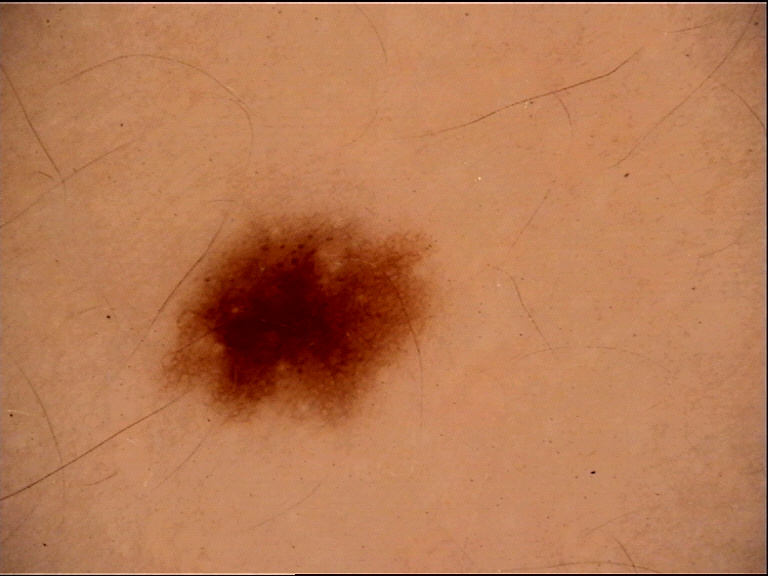Findings:
• class · dysplastic junctional nevus (expert consensus)